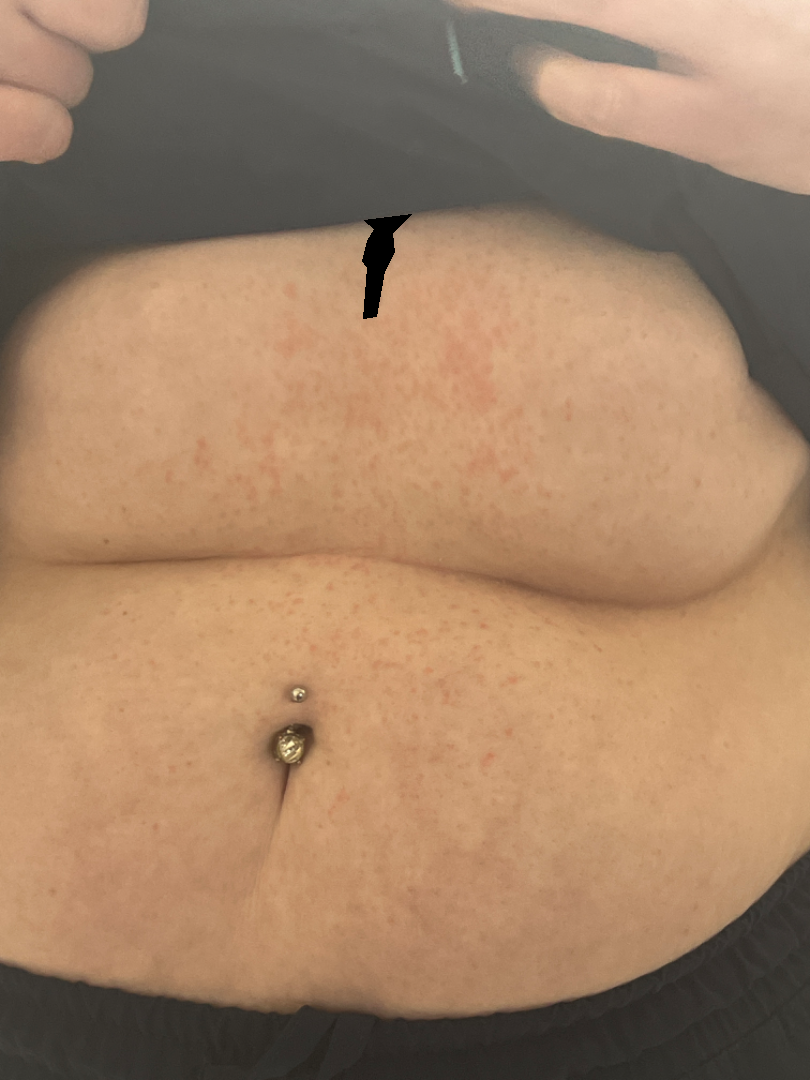systemic symptoms: none reported | subject: female, age 18–29 | history: about one day | affected area: front of the torso | self-categorized as: a rash | skin tone: lay graders estimated MST 2 or 3 | described texture: raised or bumpy | framing: at a distance | clinical impression: Drug Rash (41%); Viral Exanthem (41%); Grover's disease (18%).